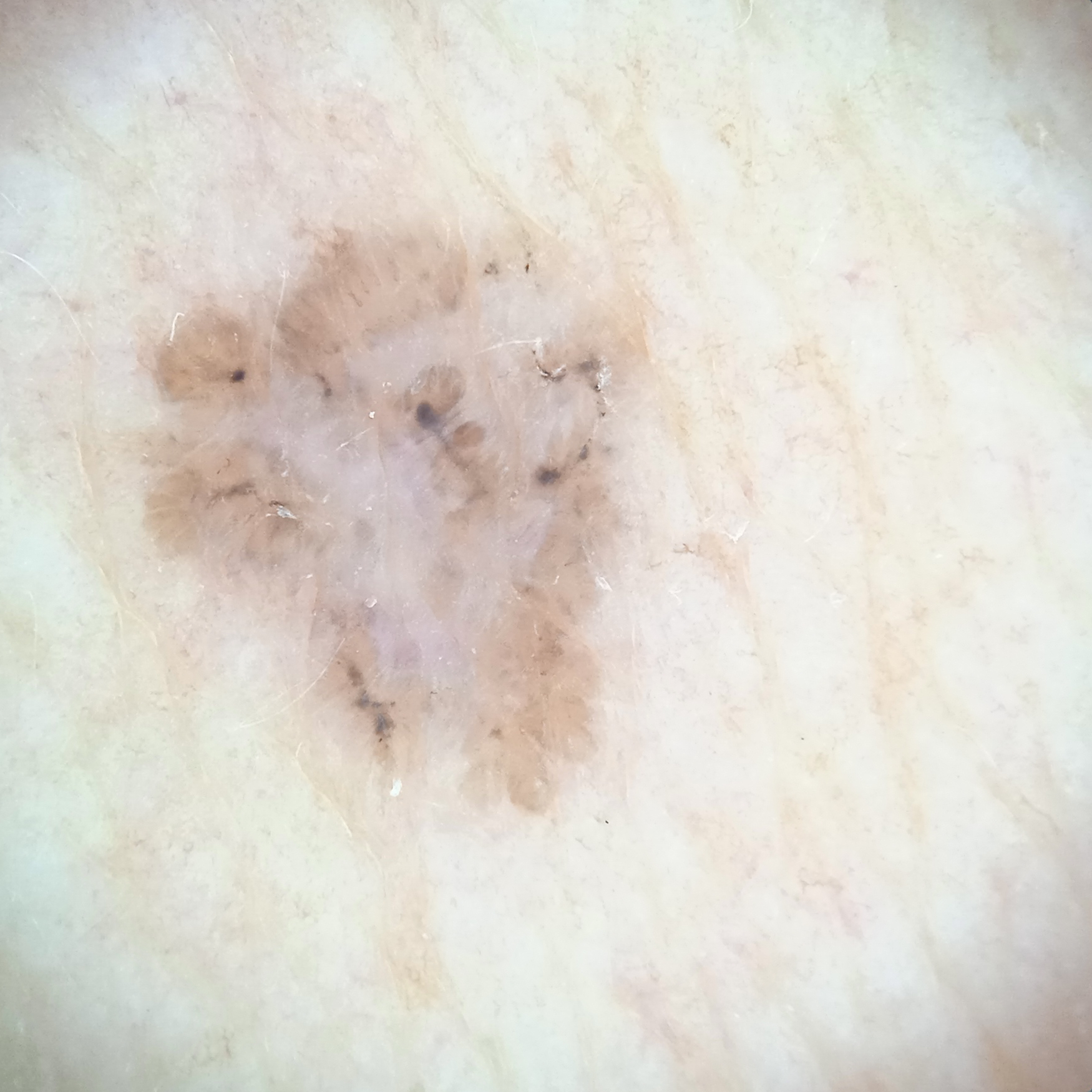<lesion>
<diagnosis>
<name>basal cell carcinoma</name>
<malignancy>malignant</malignancy>
</diagnosis>
</lesion>